The affected area is the arm; close-up view; male contributor, age 18–29:
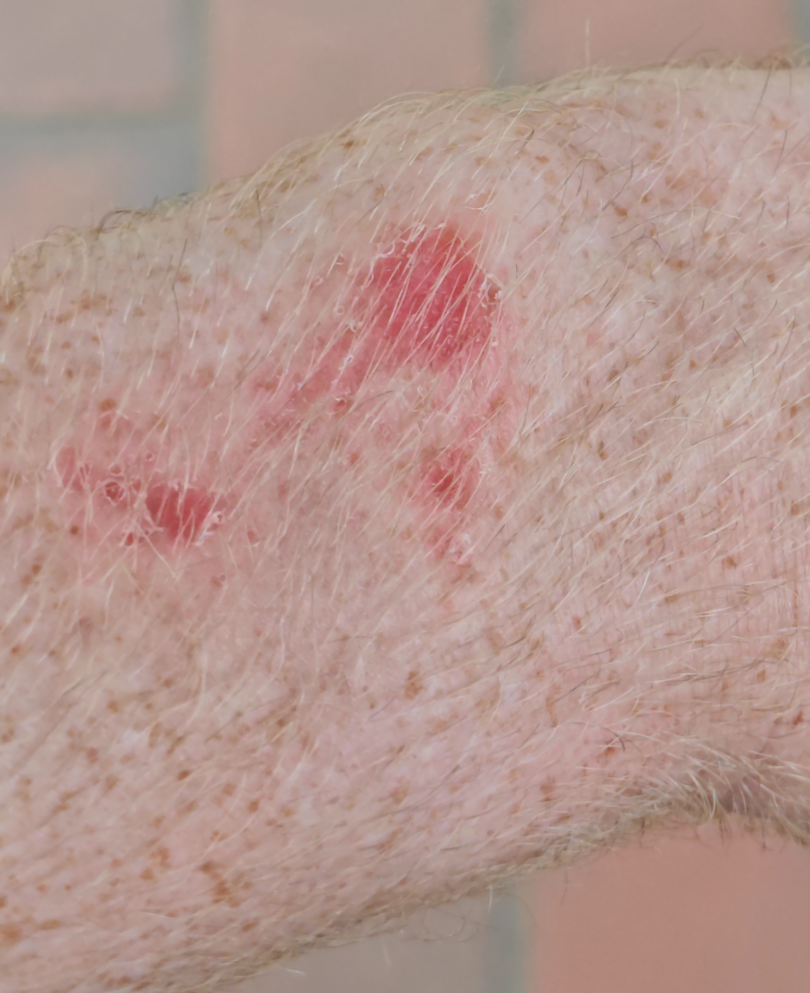present for = one to four weeks, lesion symptoms = bothersome appearance and itching, systemic symptoms = none reported, dermatologist impression = the leading consideration is Superficial wound of body region; the differential also includes SCC/SCCIS.